A dermoscopy image of a single skin lesion. A male patient aged 13-17: 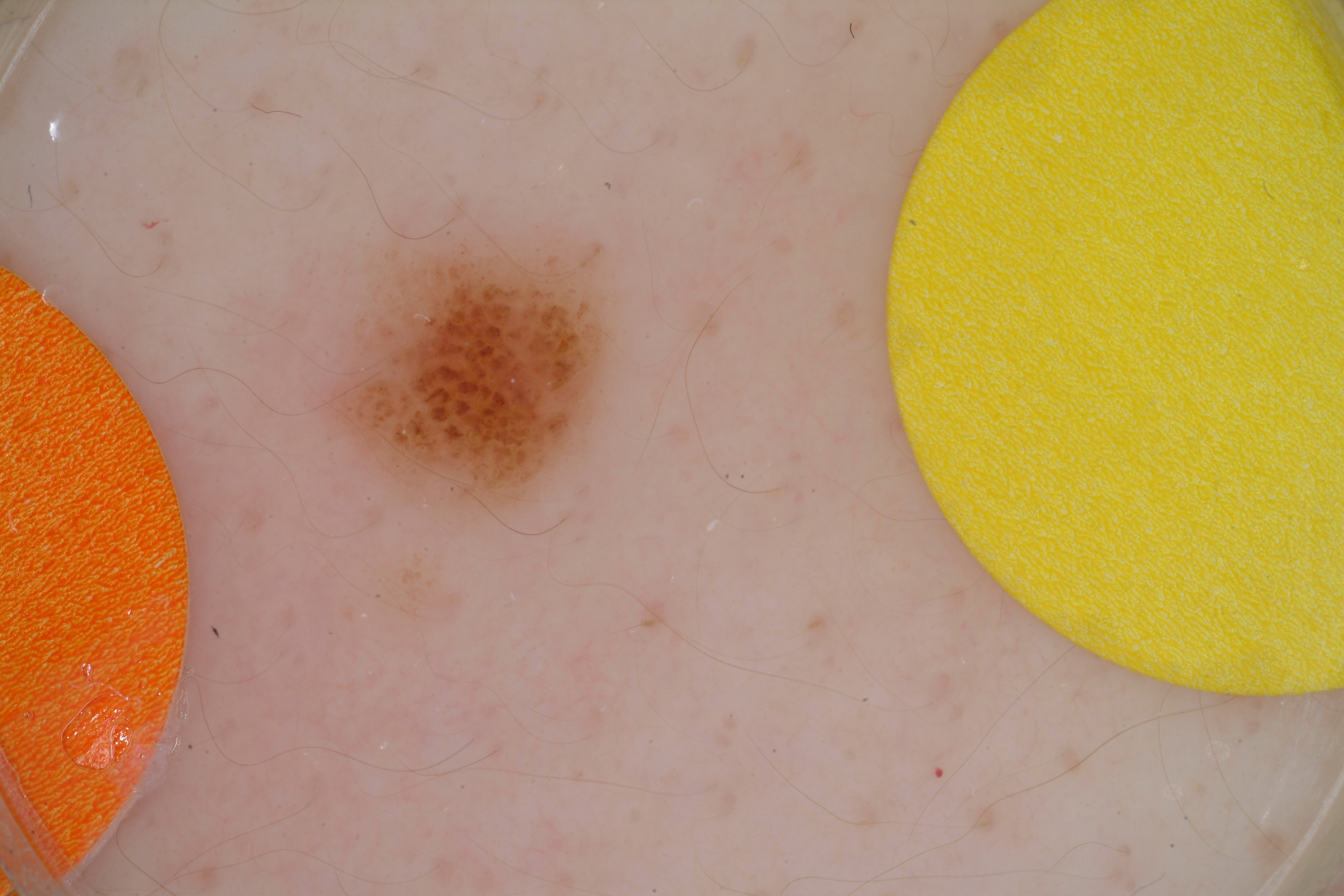* features · globules
* bounding box · 305 213 627 529
* assessment · a melanocytic nevus